This is a close-up image — 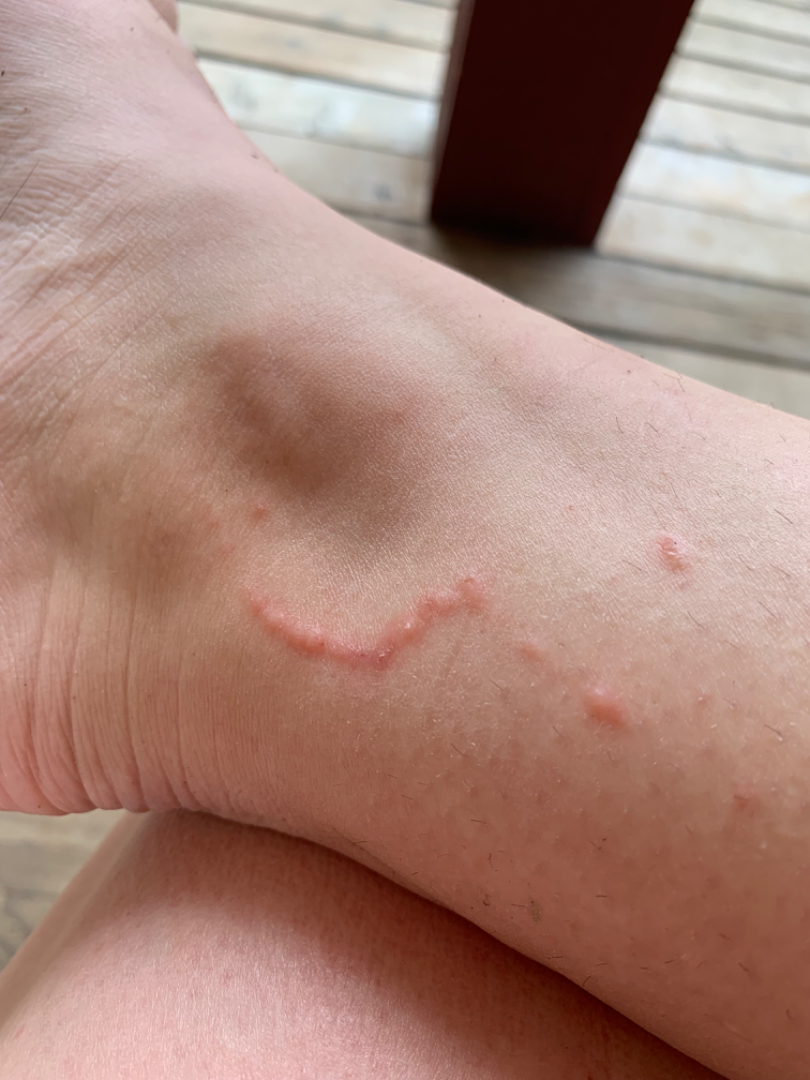The lesion is associated with itching, burning and bothersome appearance. The contributor notes the lesion is fluid-filled and raised or bumpy. The patient considered this a rash. Reported duration is one to four weeks. On dermatologist assessment of the image: in keeping with Cutaneous larva migrans.